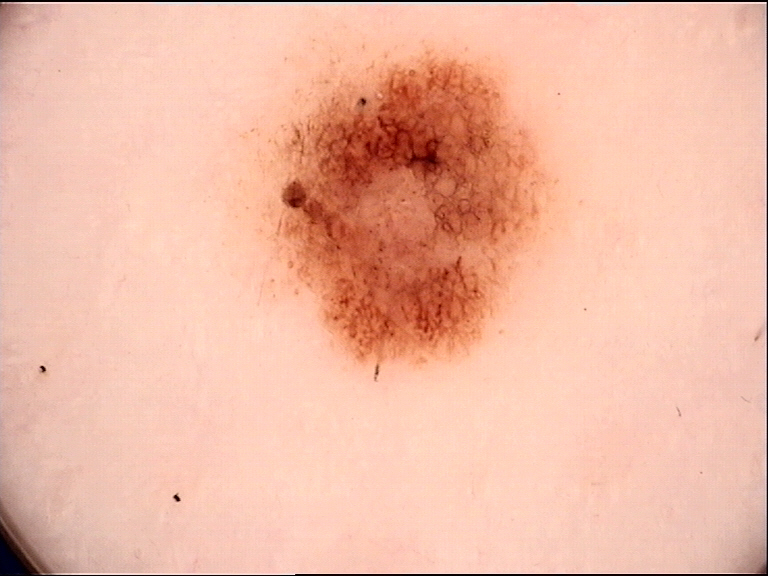A dermatoscopic image of a skin lesion.
The diagnostic label was a dysplastic junctional nevus.